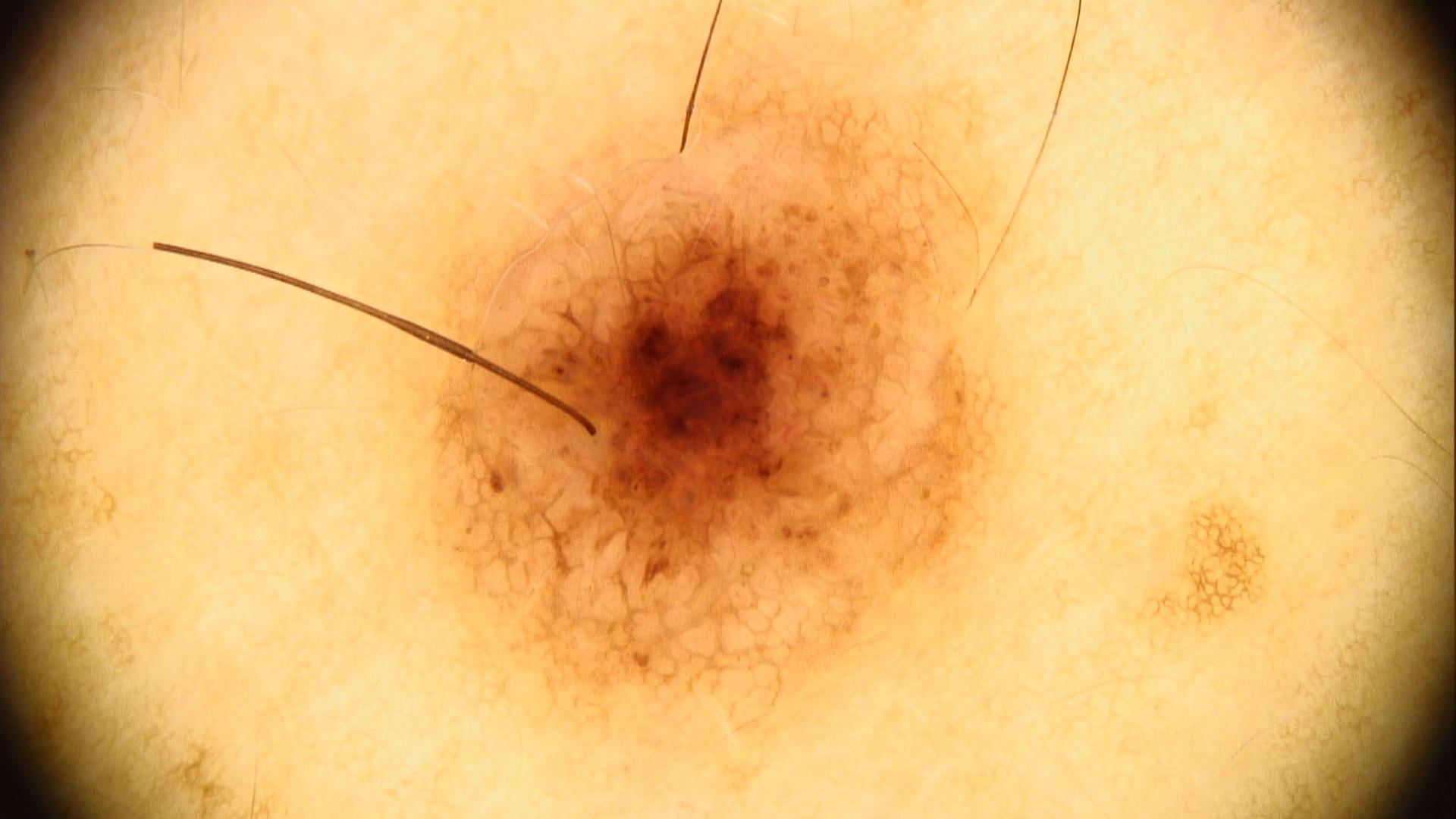image: dermatoscopic image
skin_type: III
patient:
  age_approx: 40
  sex: male
lesion_location:
  region: the trunk
  detail: the posterior trunk
diagnosis:
  name: Nevus
  malignancy: benign
  confirmation: expert clinical impression
  lineage: melanocytic